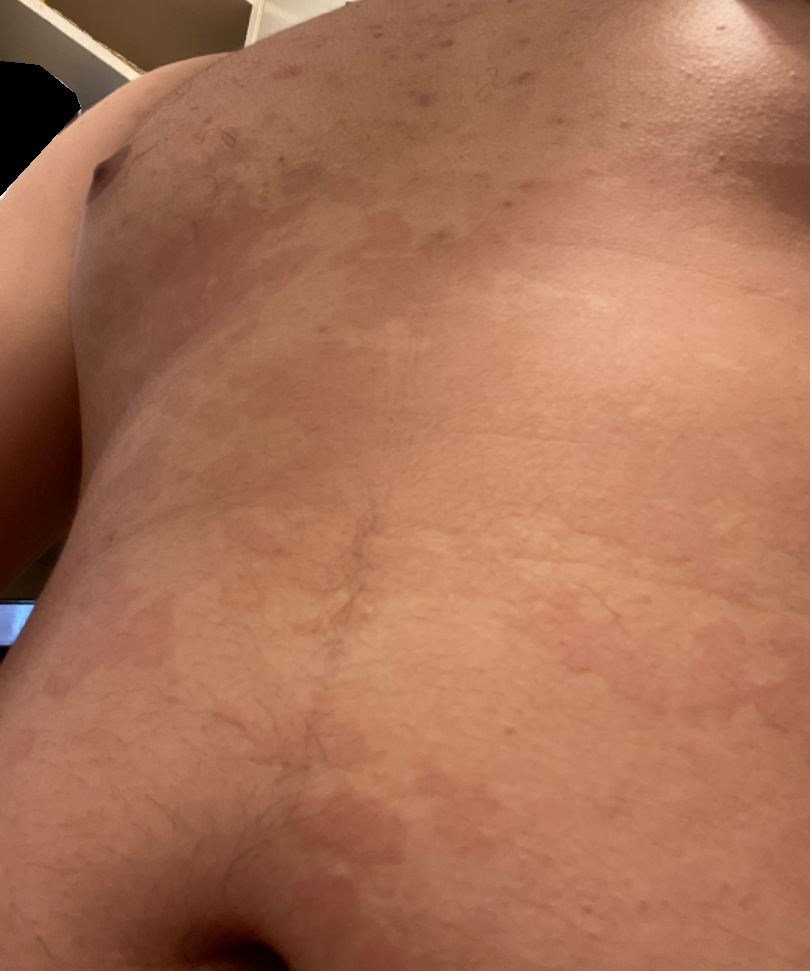subject = male, age 18–29 | affected area = back of the torso and front of the torso | shot type = at an angle | differential diagnosis = the primary impression is Tinea Versicolor; possibly Urticaria; less likely is Pityriasis rubra pilaris; a more distant consideration is Psoriasis.